A dermoscopic close-up of a skin lesion.
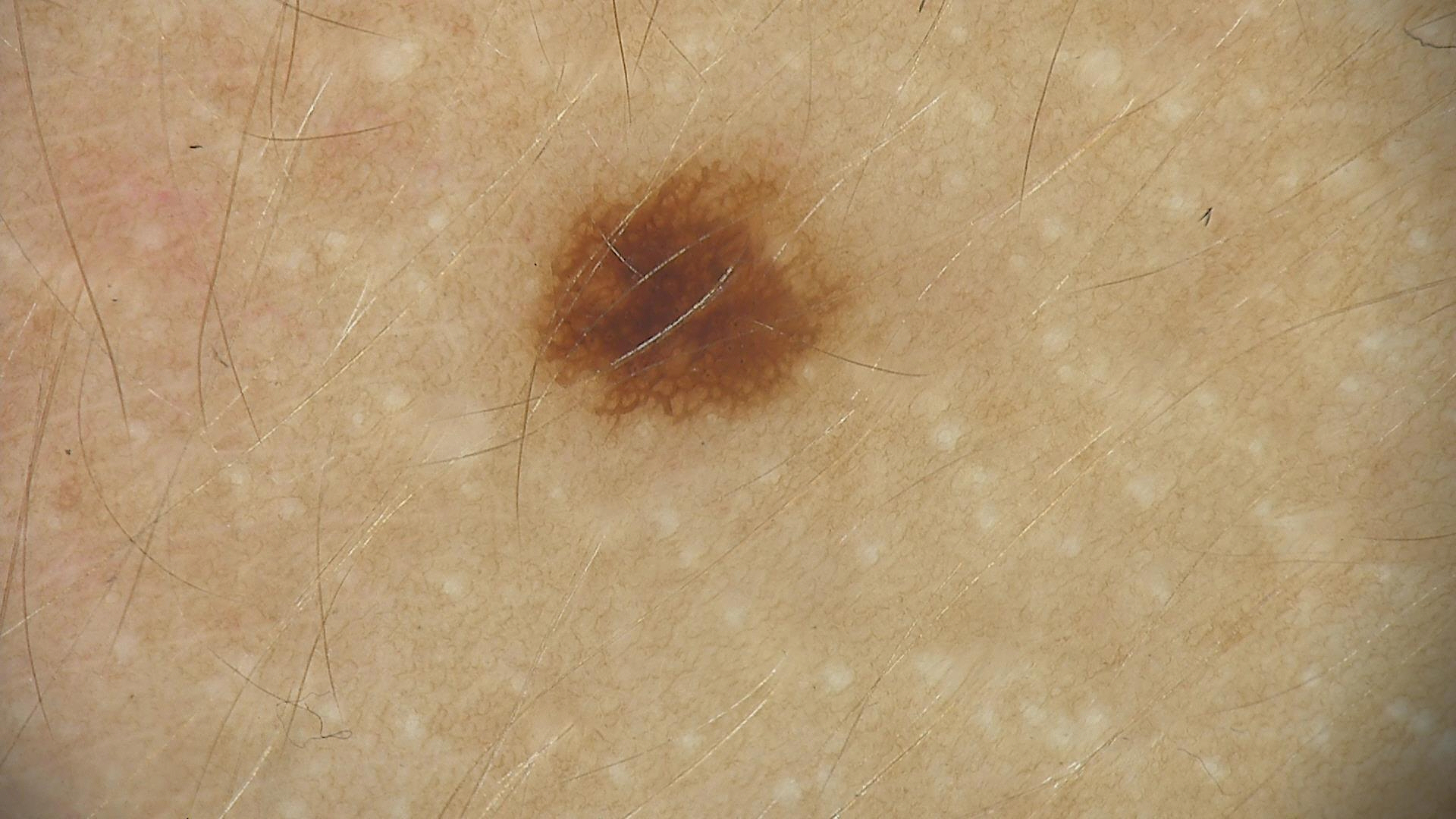  diagnosis:
    name: dysplastic junctional nevus
    code: jd
    malignancy: benign
    super_class: melanocytic
    confirmation: expert consensus